Dermoscopy of a skin lesion · a female patient in their mid- to late 80s or older: 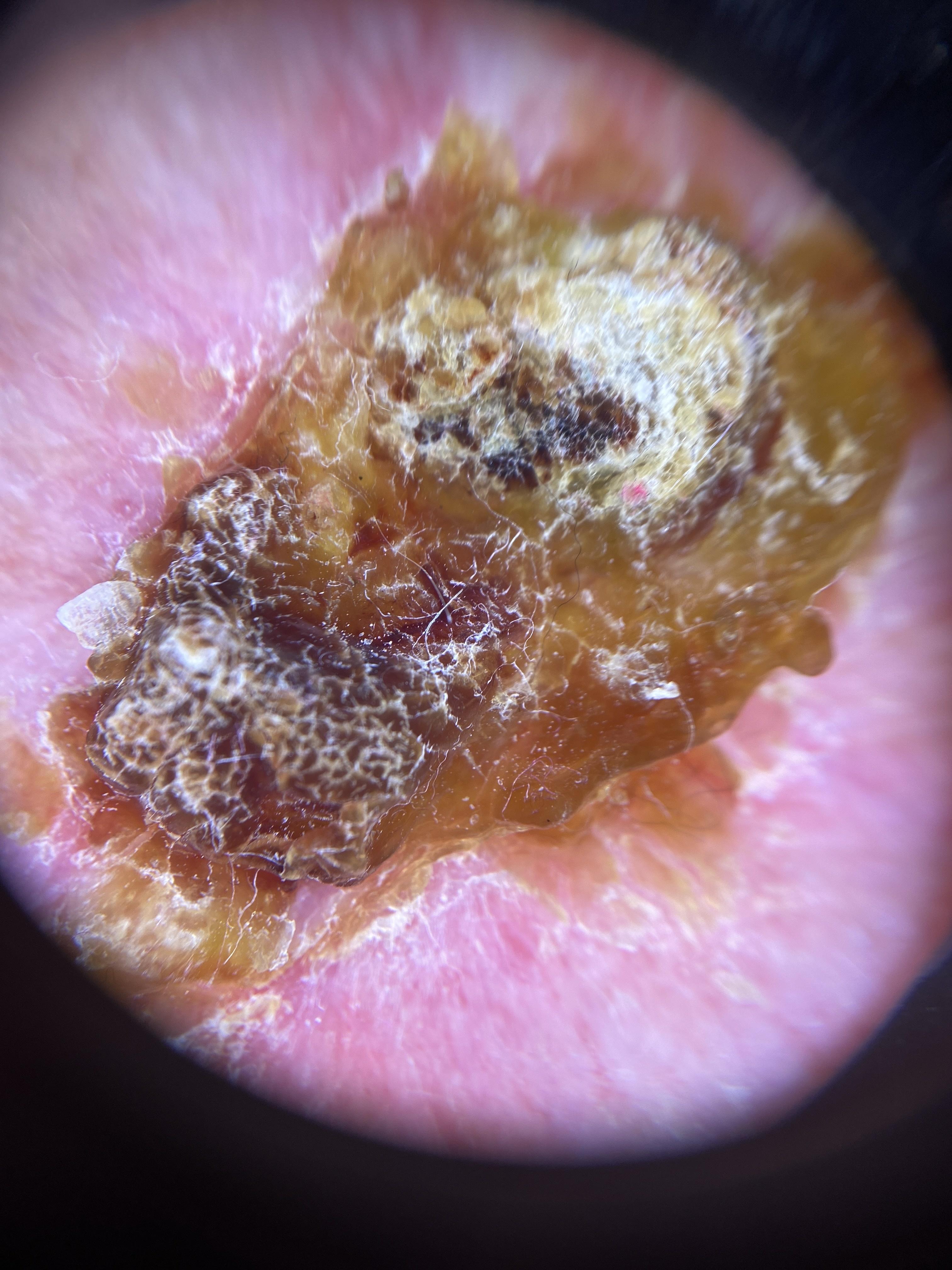location: an upper extremity; diagnosis: Basal cell carcinoma (biopsy-proven).